A dermoscopy image of a single skin lesion.
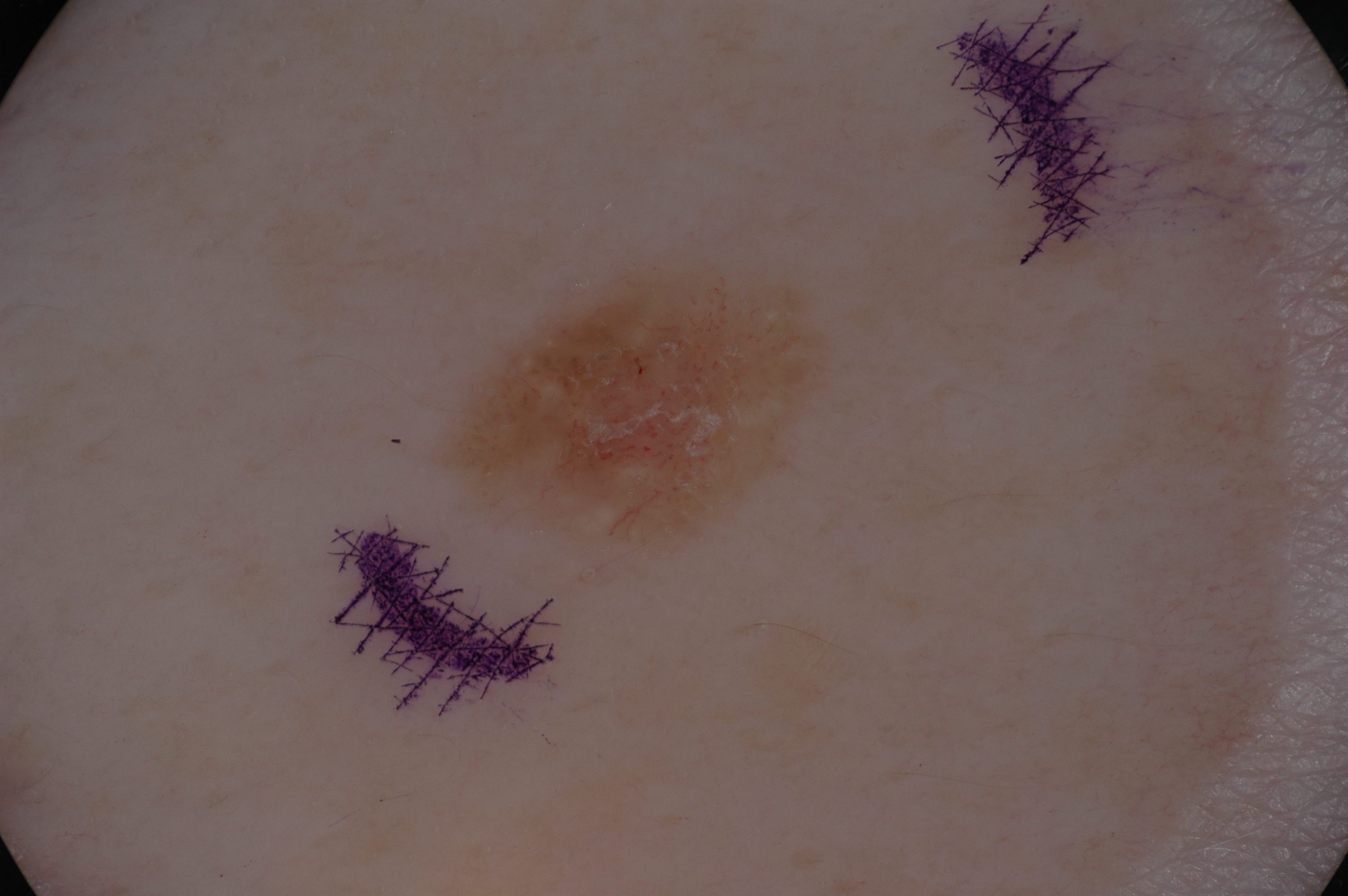location = x1=453 y1=266 x2=822 y2=539 | diagnosis = a seborrheic keratosis, a benign skin lesion.